The affected area is the back of the hand, back of the torso, front of the torso, arm, head or neck and leg; the photograph is a close-up of the affected area; the patient is female — 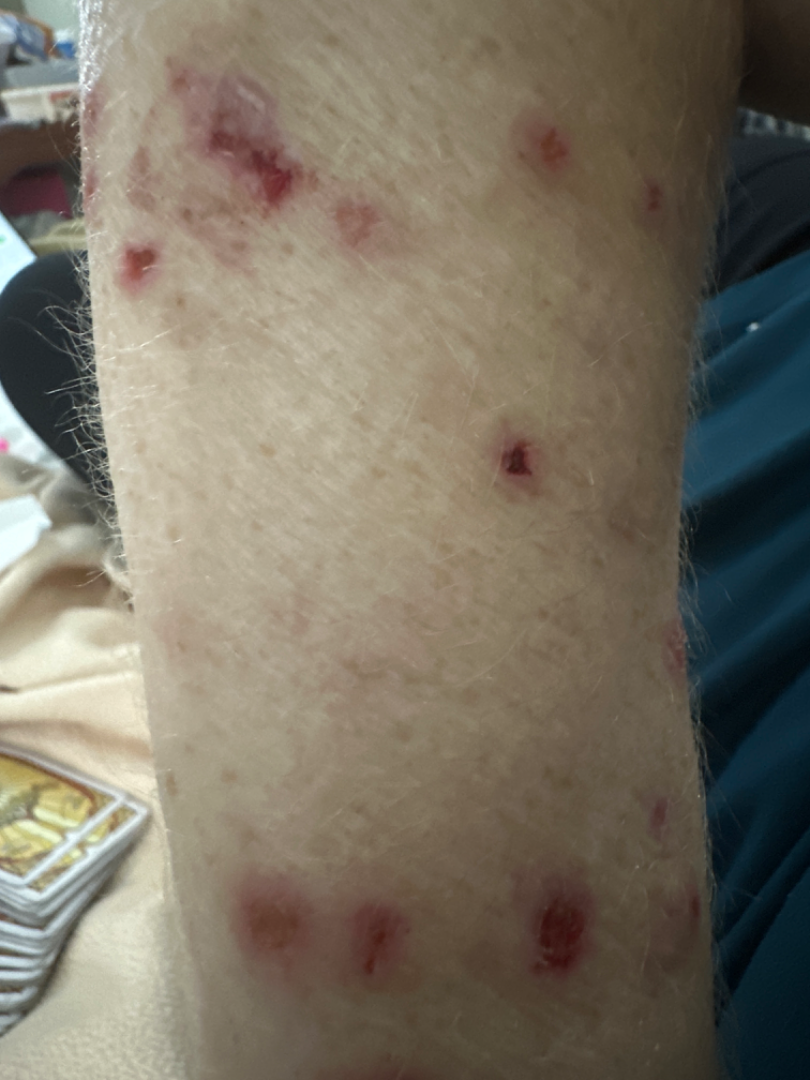skin tone = FST III; lay graders estimated Monk Skin Tone 3 (US pool) or 2 (India pool)
lesion texture = raised or bumpy and rough or flaky
associated systemic symptoms = joint pain and fatigue
patient describes the issue as = a rash
reported symptoms = bleeding, bothersome appearance and itching
differential diagnosis = single-reviewer assessment: most consistent with Prurigo